This is a close-up image · the subject is 30–39, female · the front of the torso, head or neck, back of the hand and arm are involved — 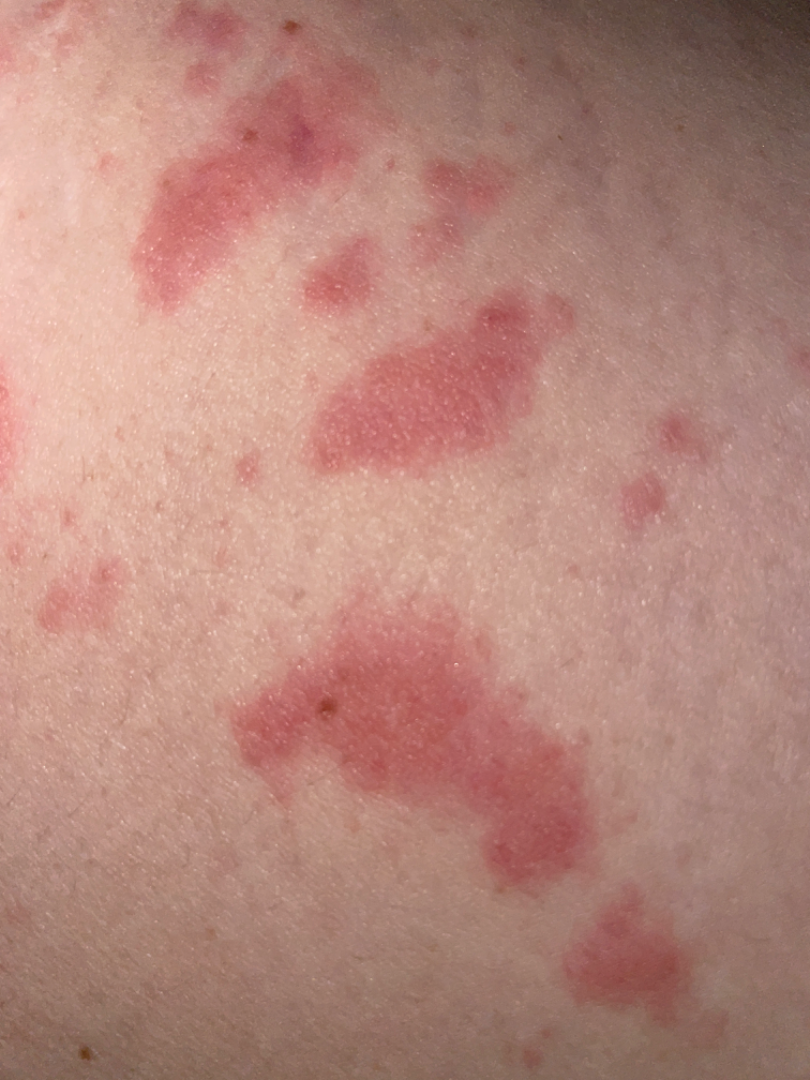Diagnostic features were not clearly distinguishable in this photograph.